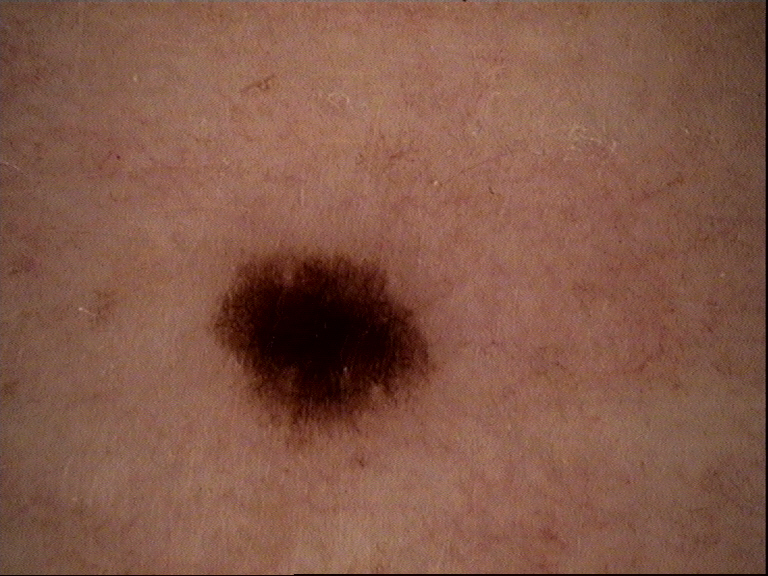image type: dermatoscopy | diagnosis: dysplastic junctional nevus (expert consensus).